An image taken at an angle. No associated systemic symptoms reported. The lesion is associated with bothersome appearance. Self-categorized by the patient as a rash. Female contributor, age 18–29. The lesion is described as raised or bumpy. The condition has been present for about one day: 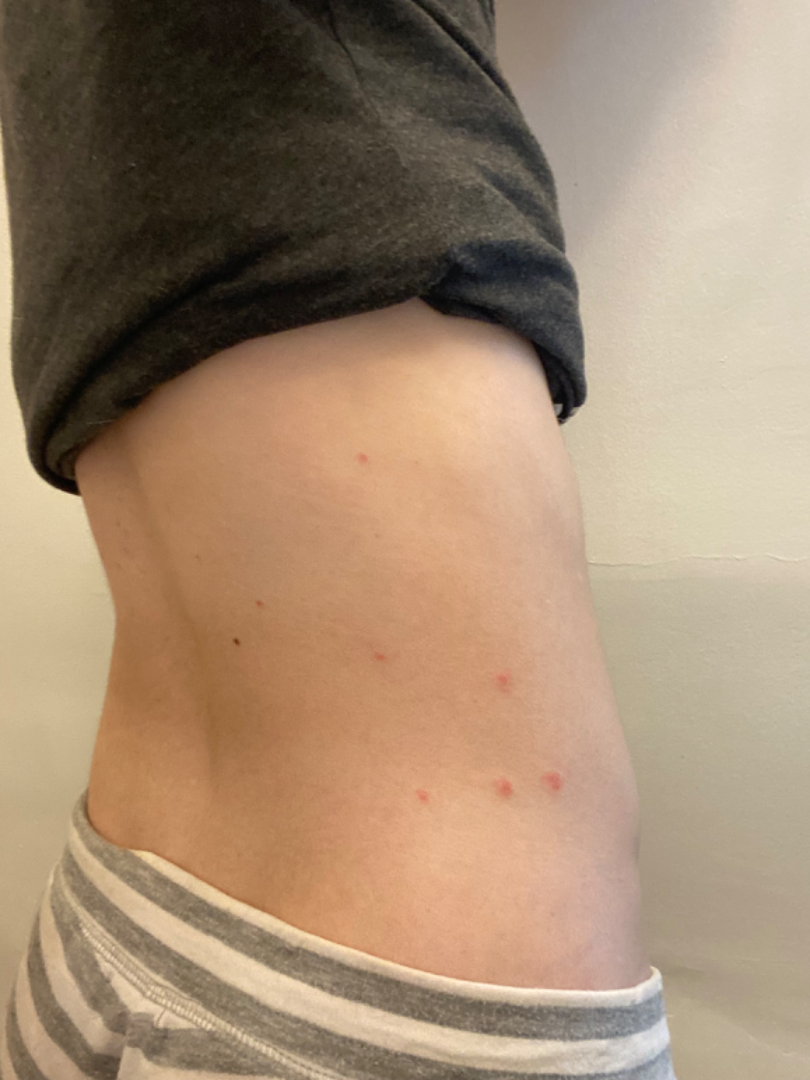The skin findings could not be characterized from the image.